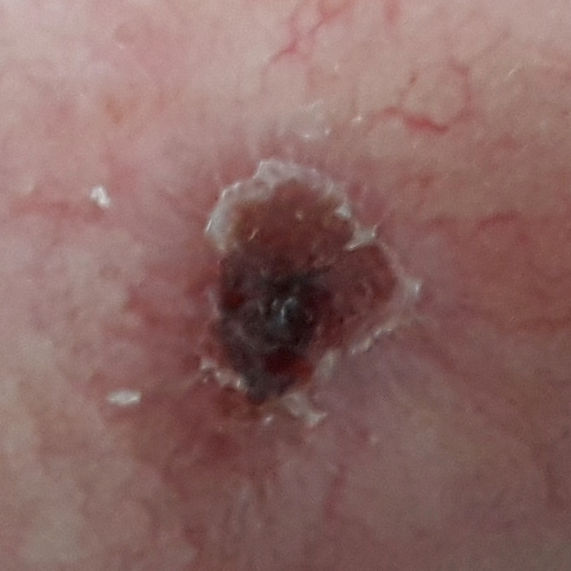Q: What does the exposure history note?
A: pesticide exposure, no prior malignancy (patient or family), no tobacco use
Q: What is the patient's skin type?
A: II
Q: What kind of image is this?
A: clinical photograph
Q: What are the lesion's dimensions?
A: 5 × 3 mm
Q: What does the patient describe?
A: bleeding, change in appearance, growth, itching, elevation
Q: What is the diagnosis?
A: basal cell carcinoma (biopsy-proven)